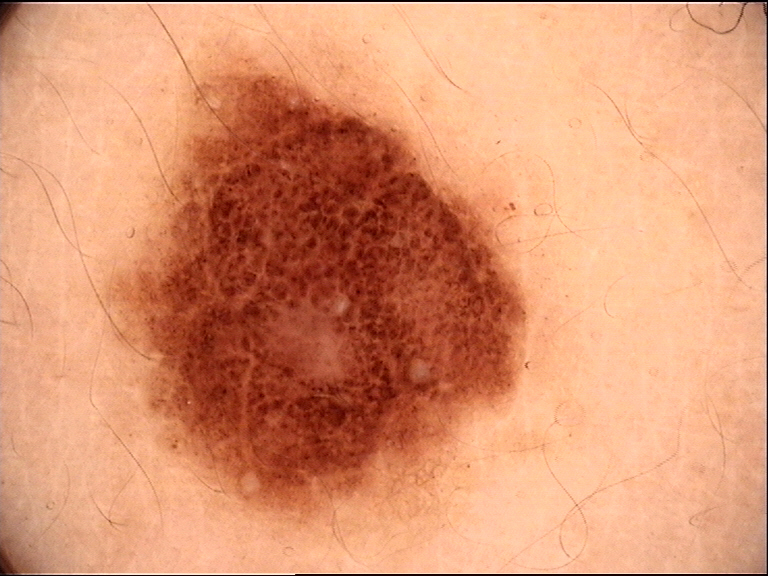A dermoscopy image of a single skin lesion. The diagnostic label was a banal lesion — a compound nevus.